The patient says their skin tans without first burning; referred for assessment of suspected basal cell carcinoma; the patient describes having few moles overall; a clinical photograph of a skin lesion — 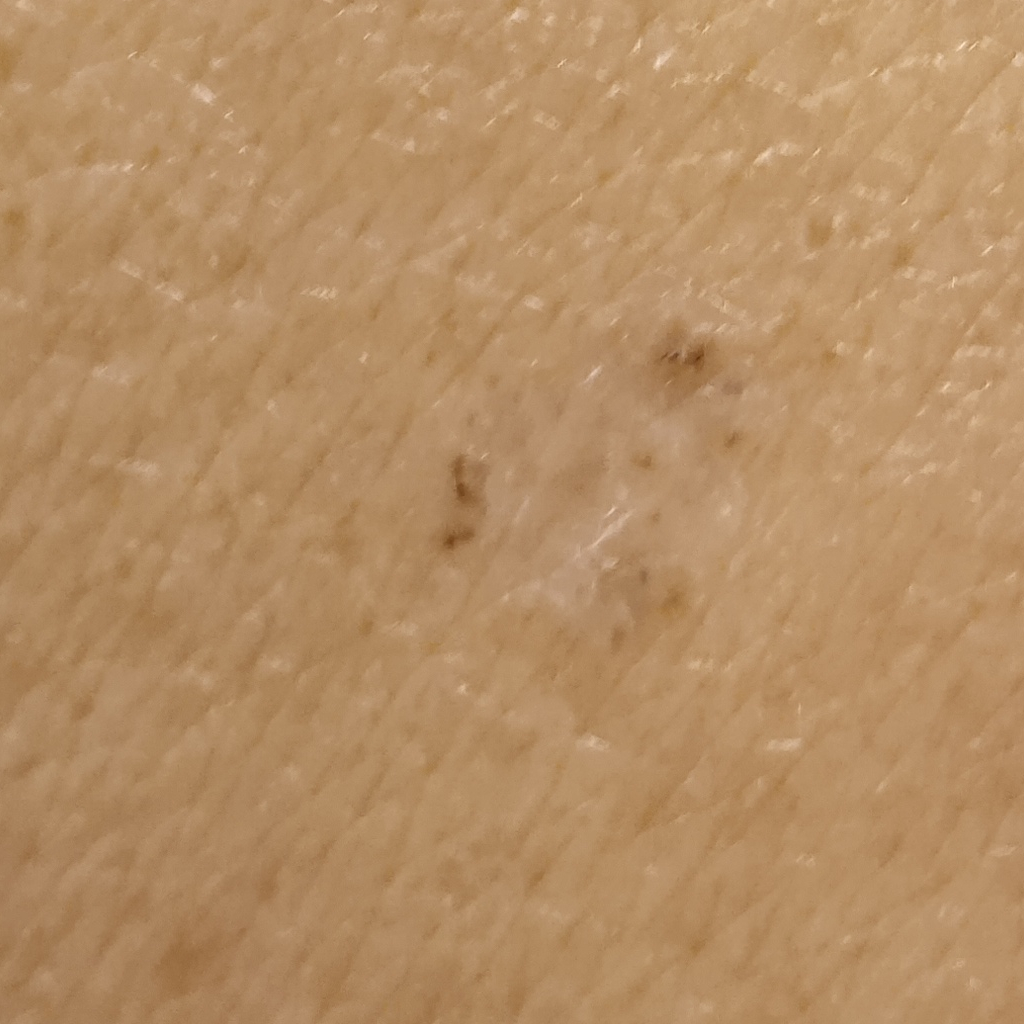The lesion is located on the back.
The lesion is about 7.8 mm across.
Dermatologist review favored a basal cell carcinoma.